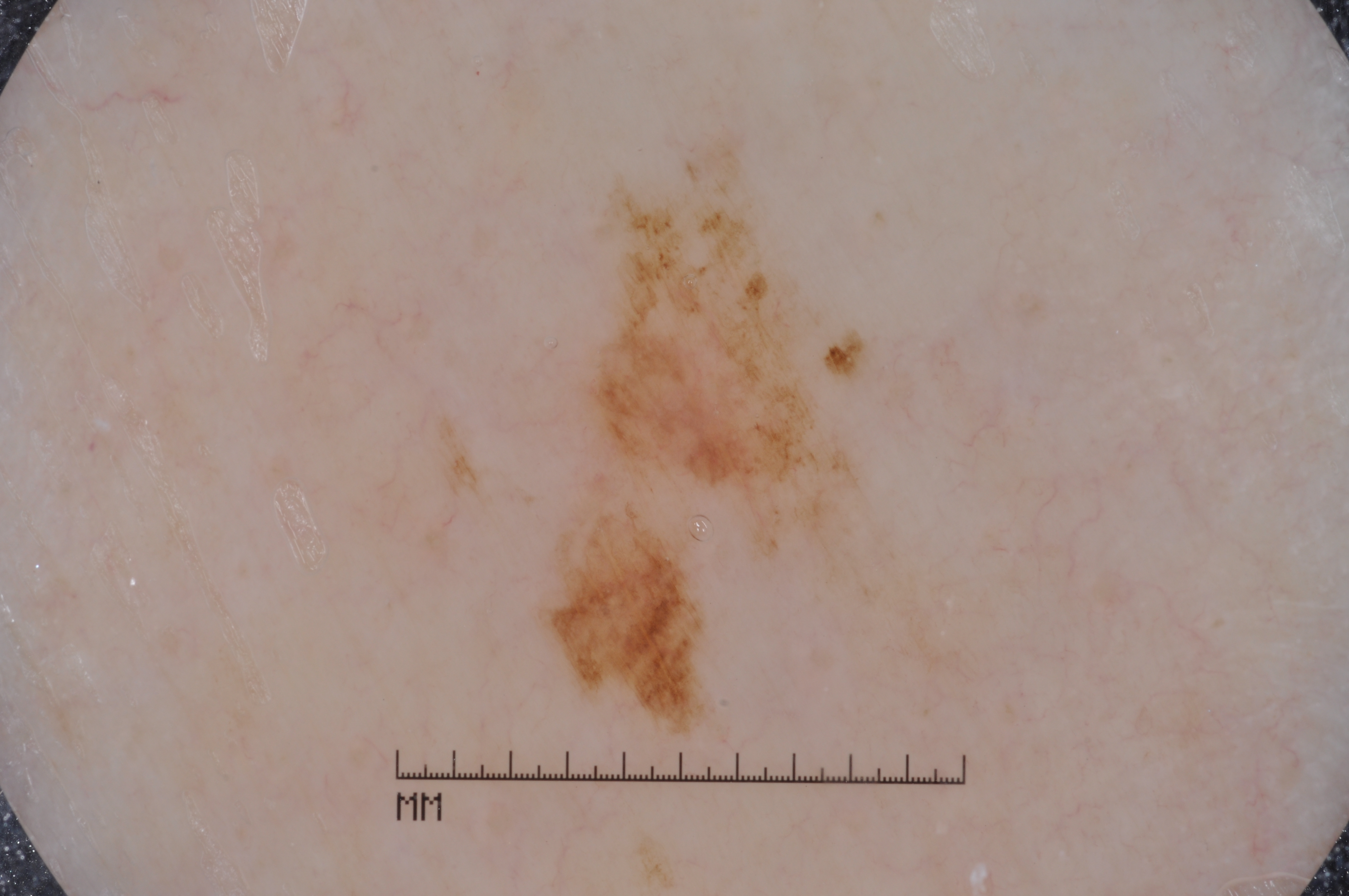<lesion>
  <image>
    <modality>dermoscopy</modality>
  </image>
  <patient>
    <sex>male</sex>
    <age_approx>60</age_approx>
  </patient>
  <lesion_extent>small</lesion_extent>
  <lesion_location>
    <bbox_xyxy>548, 175, 854, 707</bbox_xyxy>
  </lesion_location>
  <dermoscopic_features>
    <present/>
    <absent>pigment network, streaks, milia-like cysts, negative network</absent>
  </dermoscopic_features>
  <diagnosis>
    <name>melanoma</name>
    <malignancy>malignant</malignancy>
    <lineage>melanocytic</lineage>
    <provenance>histopathology</provenance>
  </diagnosis>
</lesion>